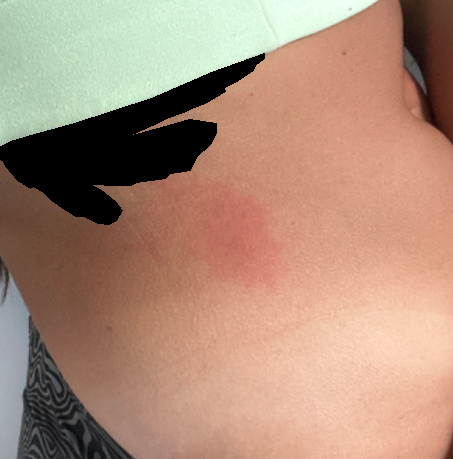Impression: The condition could not be reliably identified from the image.